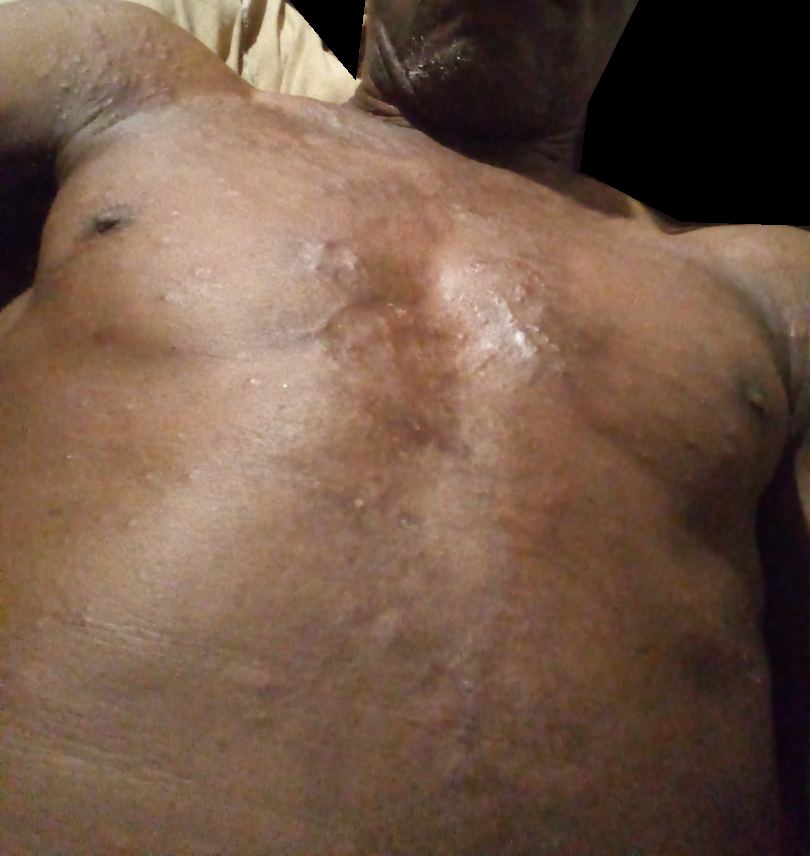assessment: not assessable
image framing: close-up
site: front of the torso, head or neck and arm